The chart records a prior melanoma · a male subject aged 68 to 72 · skin type II — 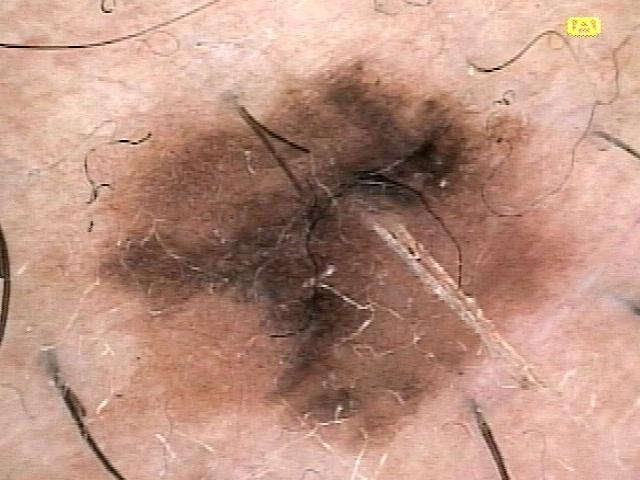Case:
- anatomic site — an upper extremity
- diagnostic label — Nevus (biopsy-proven)